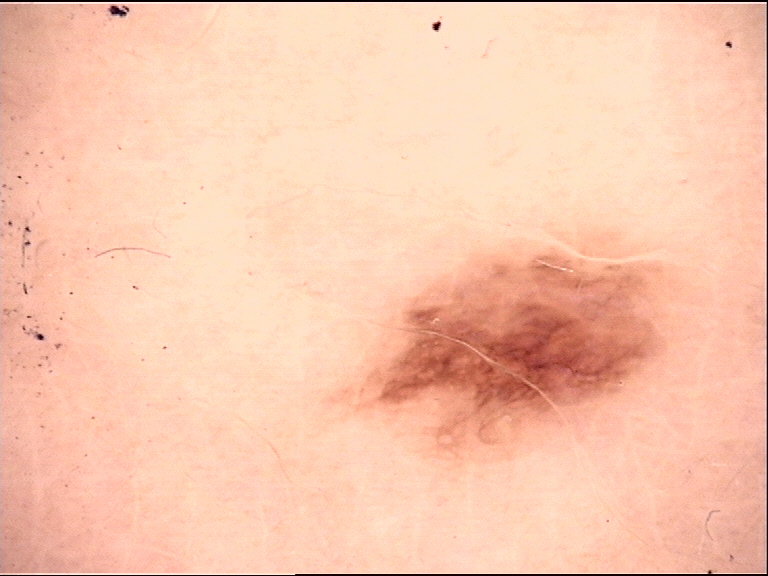A dermoscopic close-up of a skin lesion. Diagnosed as a benign lesion — a dysplastic junctional nevus.